A skin lesion imaged with a dermatoscope.
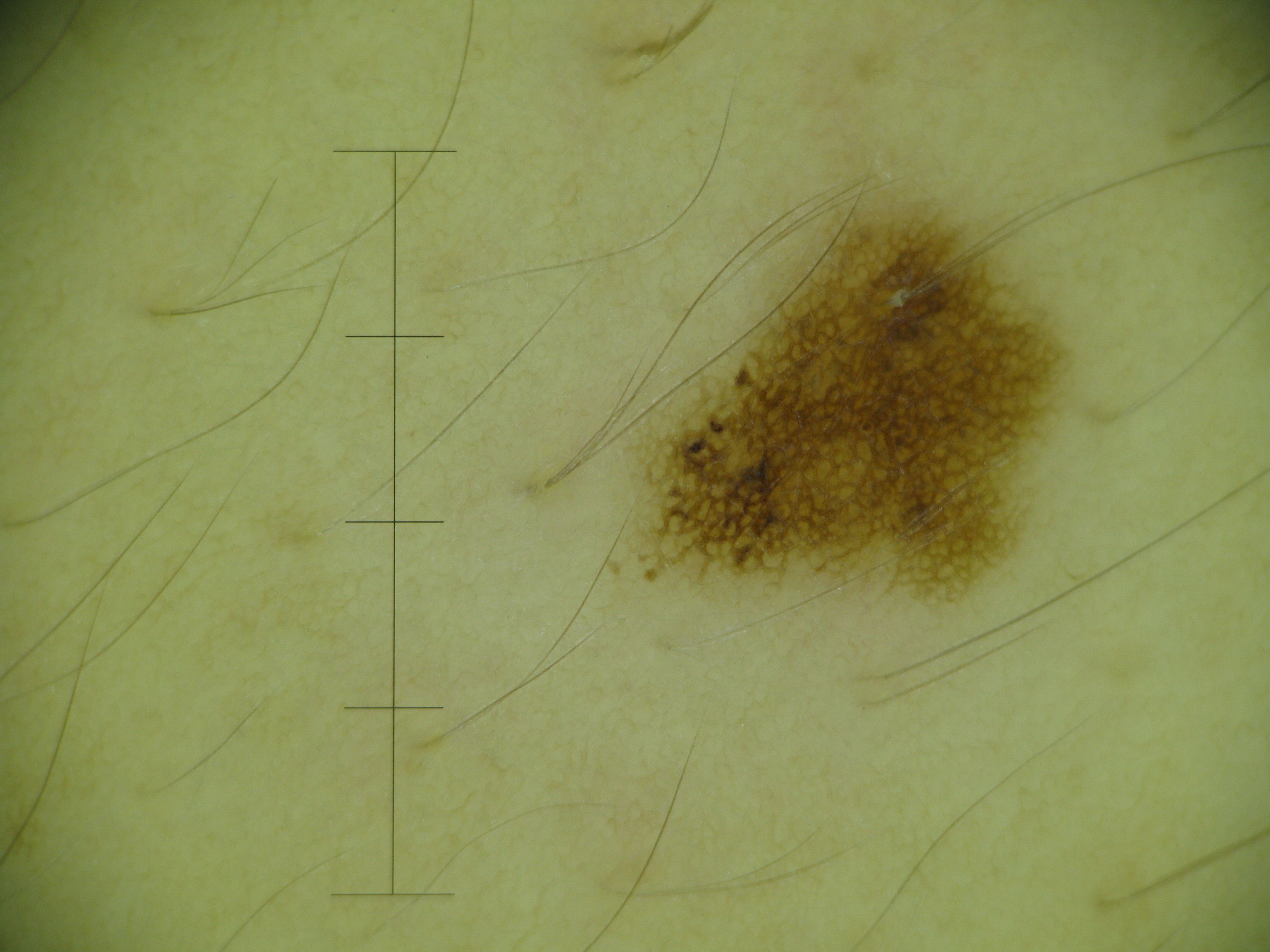assessment = dysplastic junctional nevus (expert consensus).